Present for one to three months. The contributor notes darkening, bothersome appearance and itching. The lesion is described as raised or bumpy and rough or flaky. Close-up view.
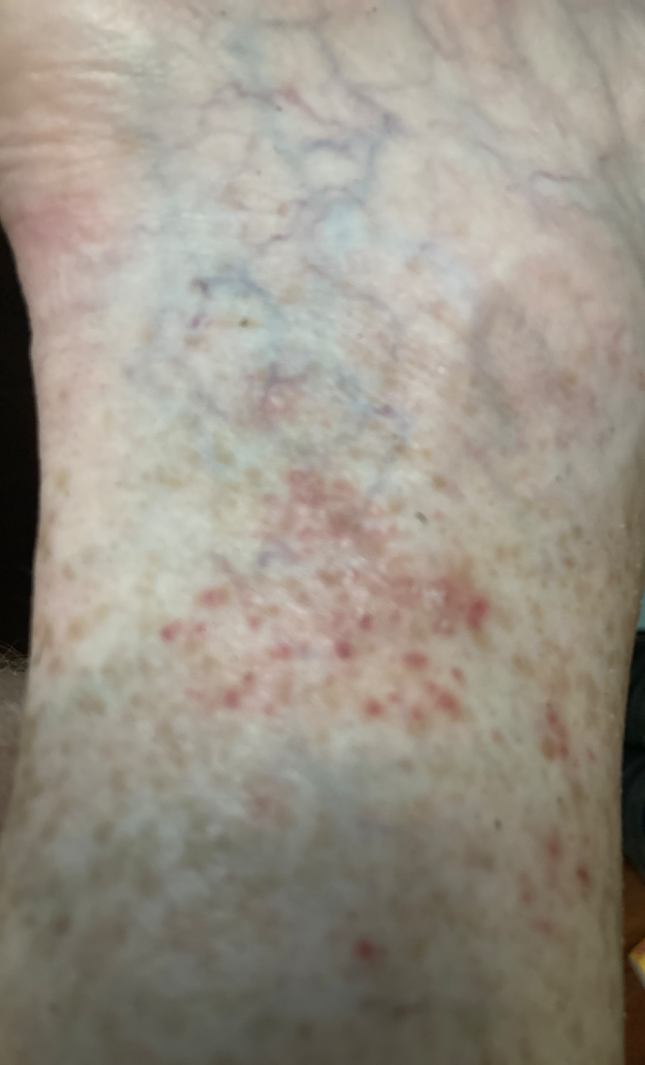| key | value |
|---|---|
| diagnostic considerations | most consistent with Pigmented purpuric eruption |